A skin lesion imaged with a dermatoscope:
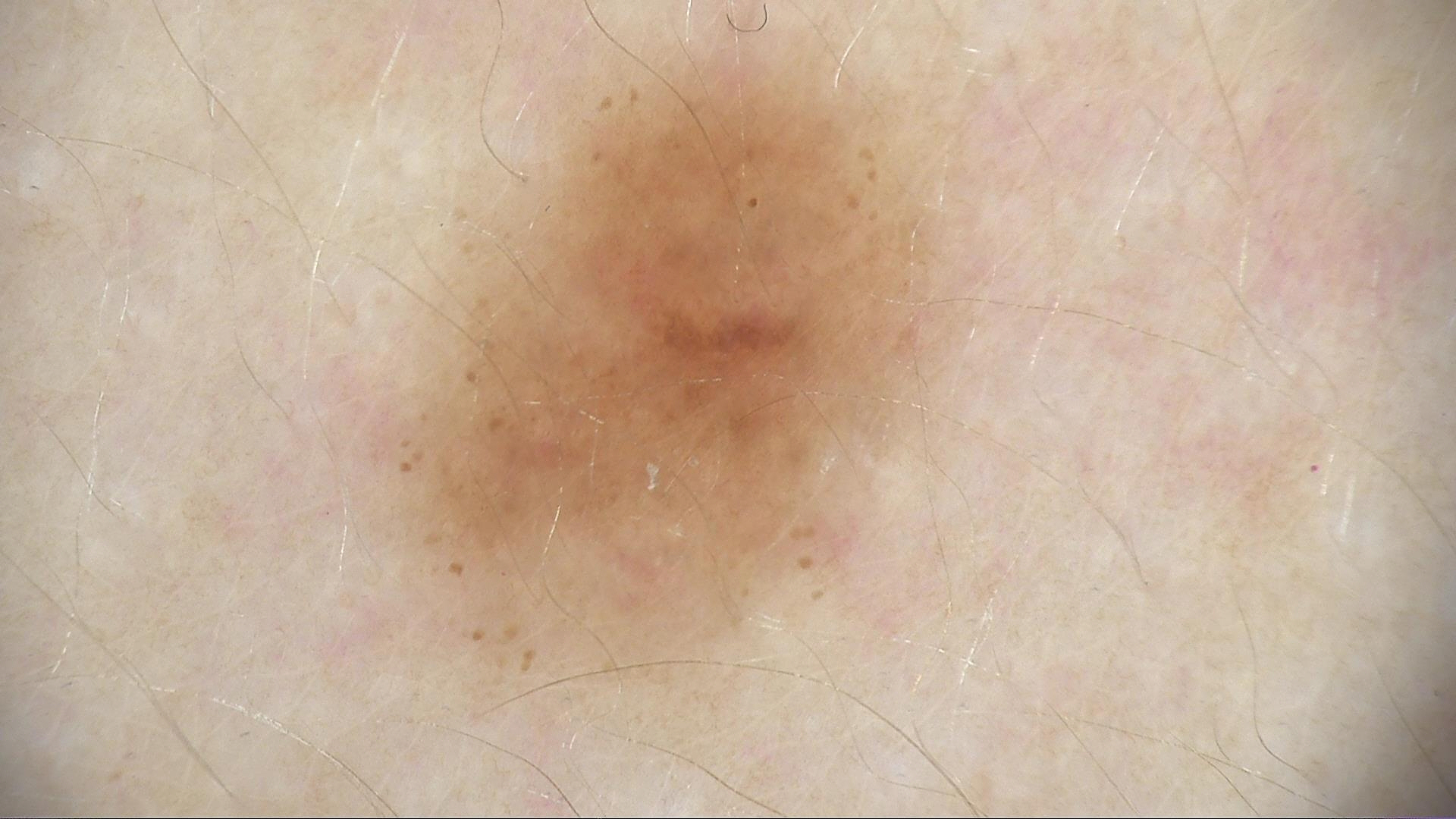Consistent with a benign lesion — a dysplastic junctional nevus.